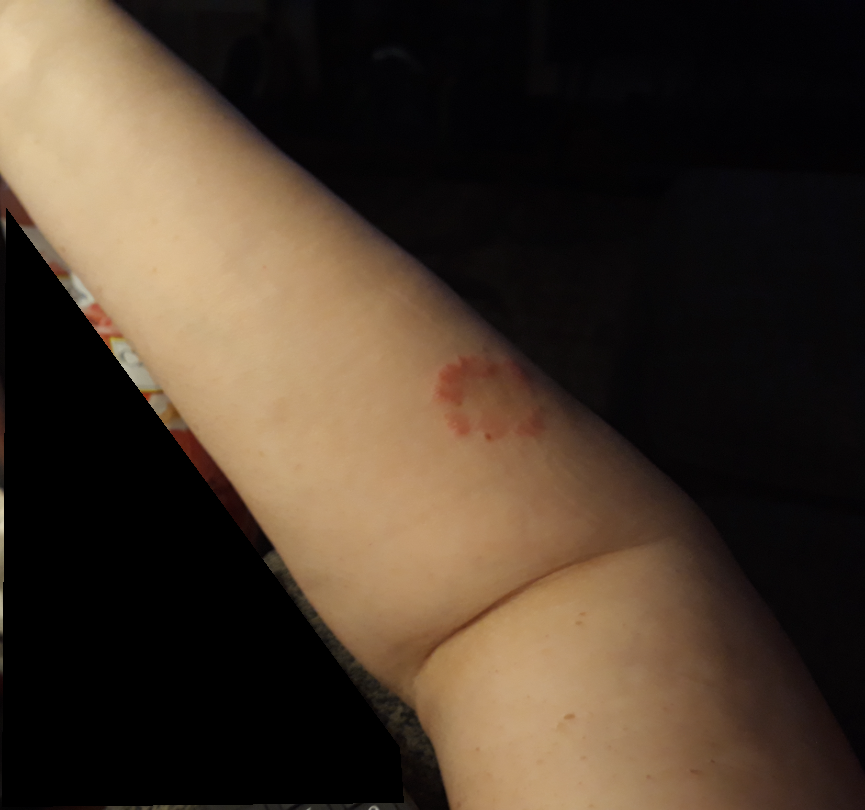The reviewer was unable to grade this case for skin condition.
Present for one to four weeks.
The lesion involves the arm.
The contributor reports itching.
Texture is reported as raised or bumpy.
This image was taken at a distance.
The patient is a female aged 60–69.